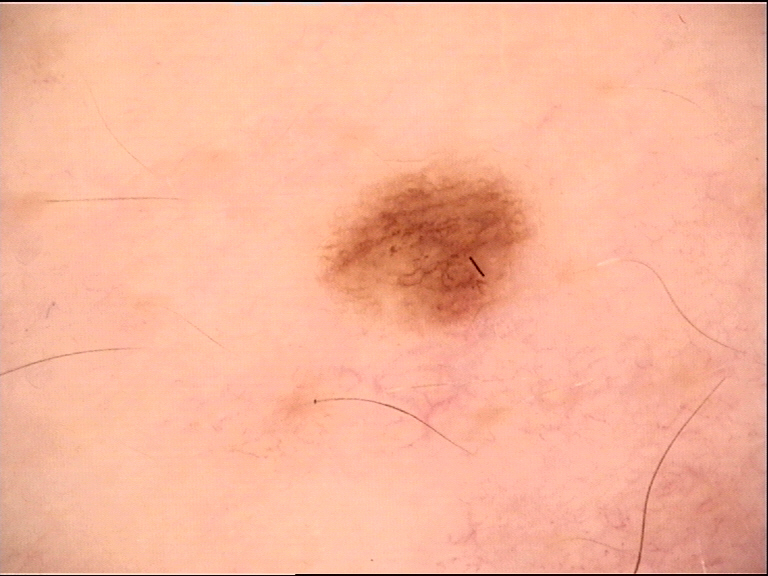Summary: A dermoscopy image of a single skin lesion. Conclusion: Diagnosed as a dysplastic junctional nevus.